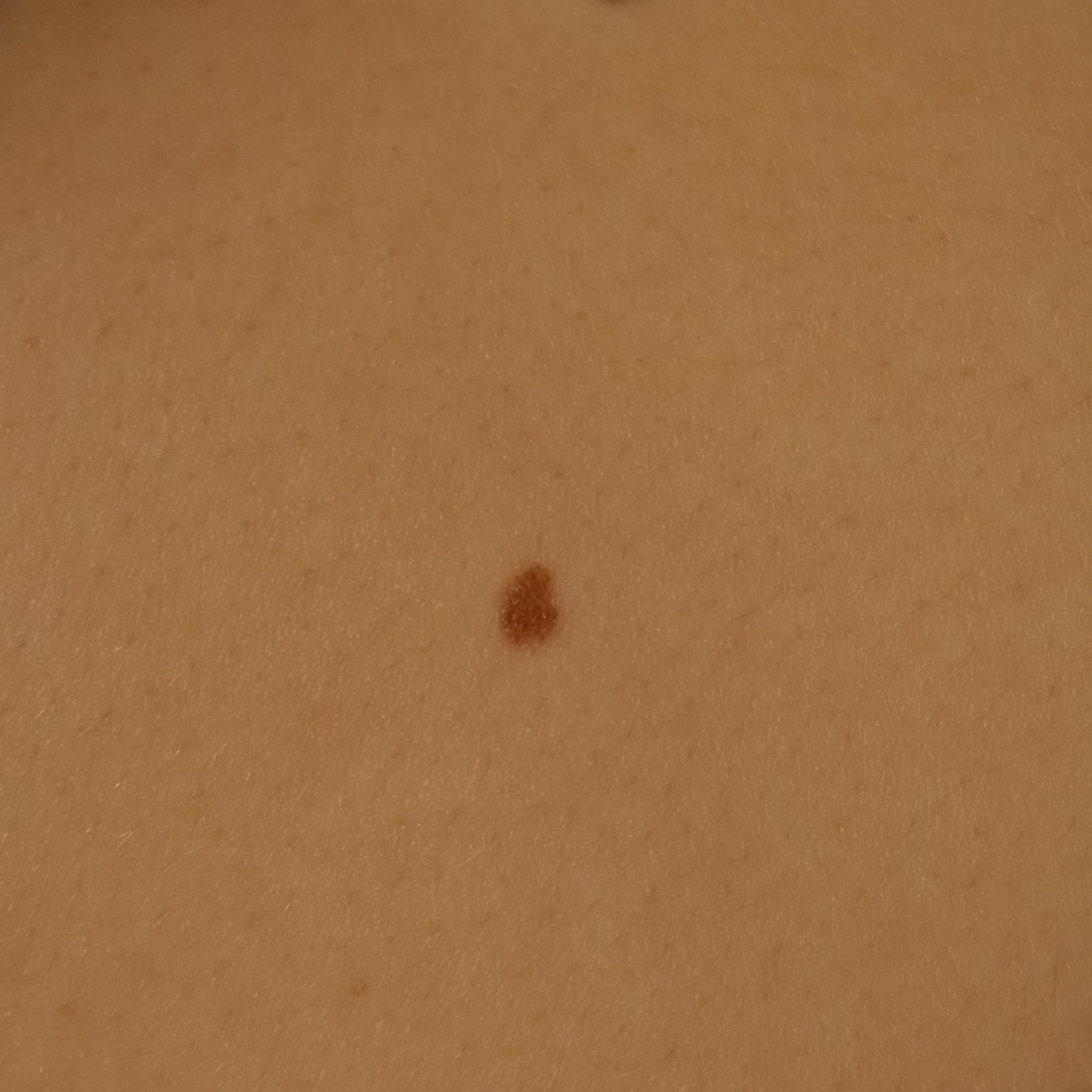Q: What was the diagnosis?
A: melanocytic nevus (dermatologist consensus)